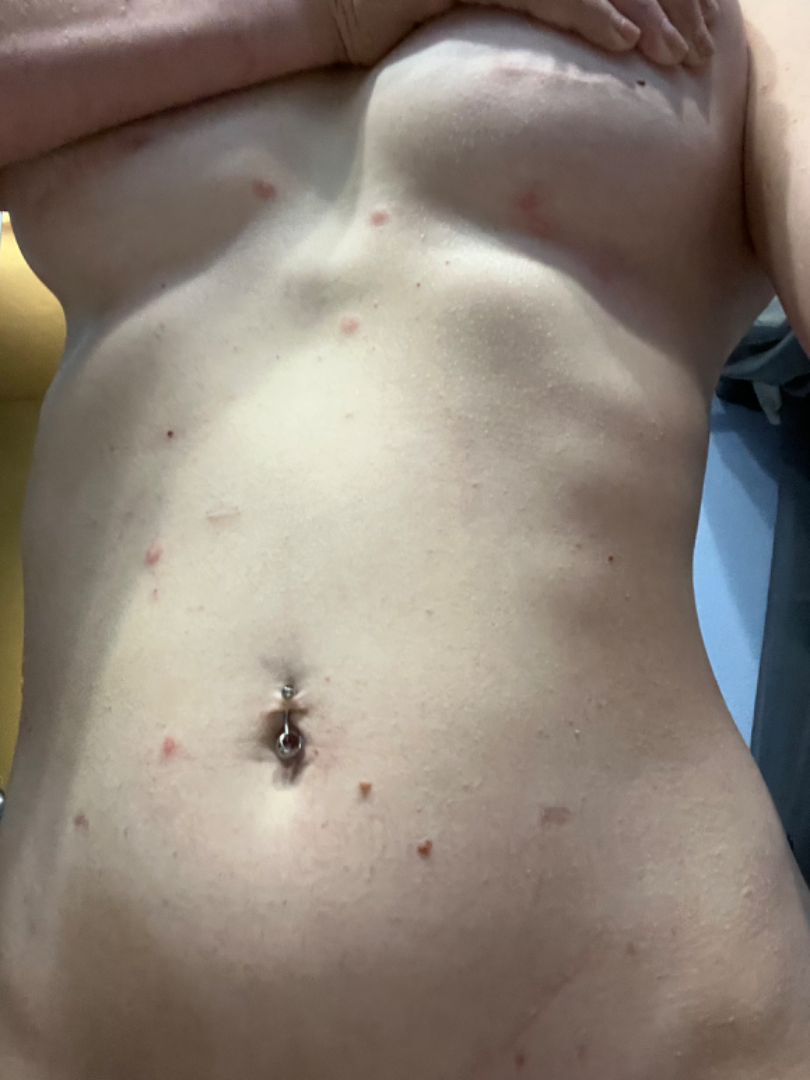History: Human graders estimated a Monk Skin Tone of 2. An image taken at a distance. The patient indicates the lesion is fluid-filled and raised or bumpy. Female patient, age 30–39. No relevant systemic symptoms. The front of the torso is involved. Impression: The leading consideration is Insect Bite.